The affected area is the leg · an image taken at an angle · the contributor reports the lesion is raised or bumpy · the patient is a female aged 40–49 · the patient described the issue as a rash · the condition has been present for about one day: 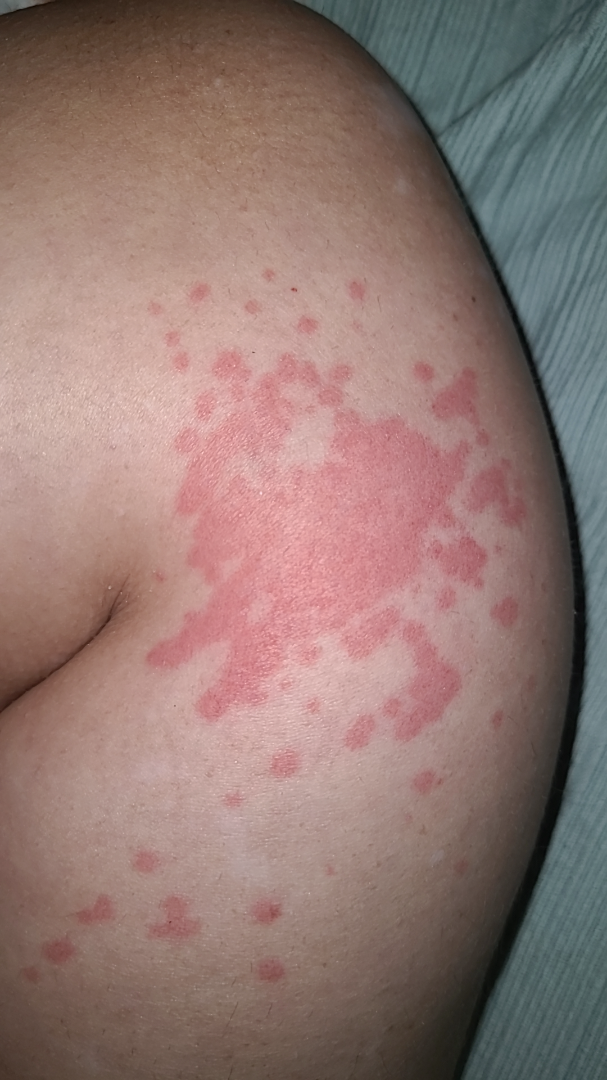The differential, in no particular order, includes Urticaria, Insect Bite and Allergic Contact Dermatitis.